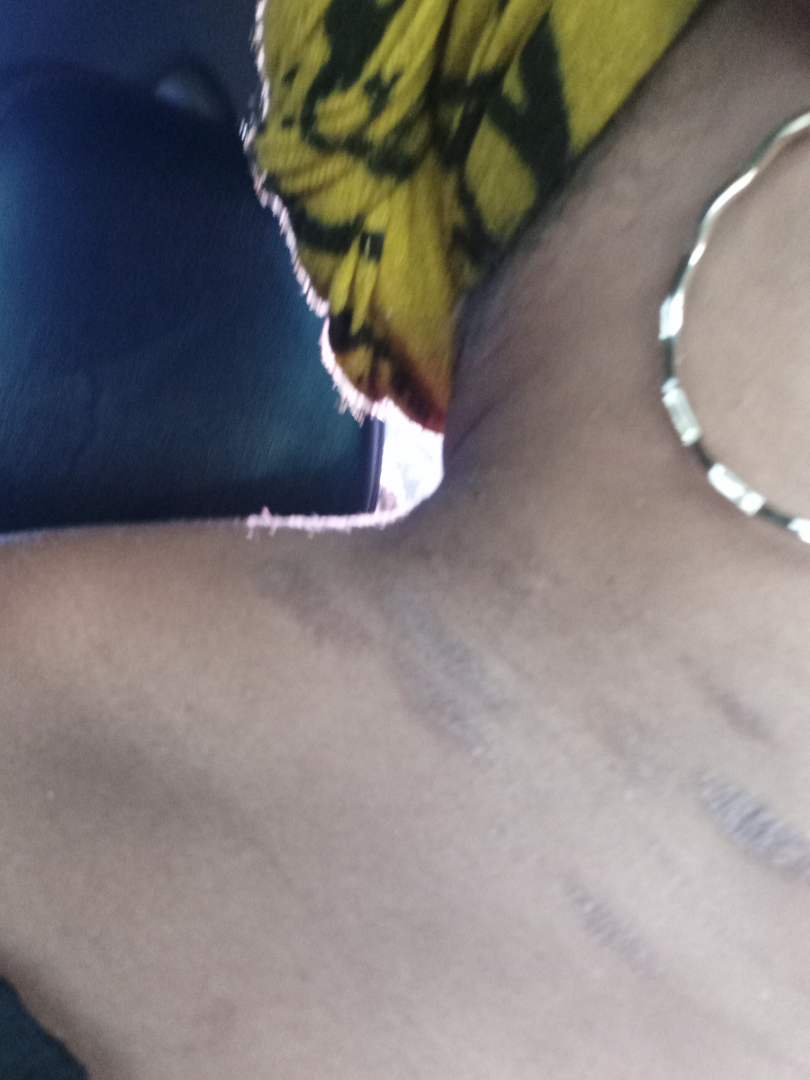<dermatology_case>
  <patient_category>skin that appeared healthy to them</patient_category>
  <duration>one to three months</duration>
  <body_site>head or neck, arm</body_site>
  <skin_tone>
    <fitzpatrick>V</fitzpatrick>
  </skin_tone>
  <patient>female, age 40–49</patient>
  <texture>flat</texture>
  <shot_type>close-up</shot_type>
  <systemic_symptoms>none reported</systemic_symptoms>
  <differential>Lichen planus/lichenoid eruption, Eczema, Allergic Contact Dermatitis</differential>
</dermatology_case>